A skin lesion imaged with contact-polarized dermoscopy: 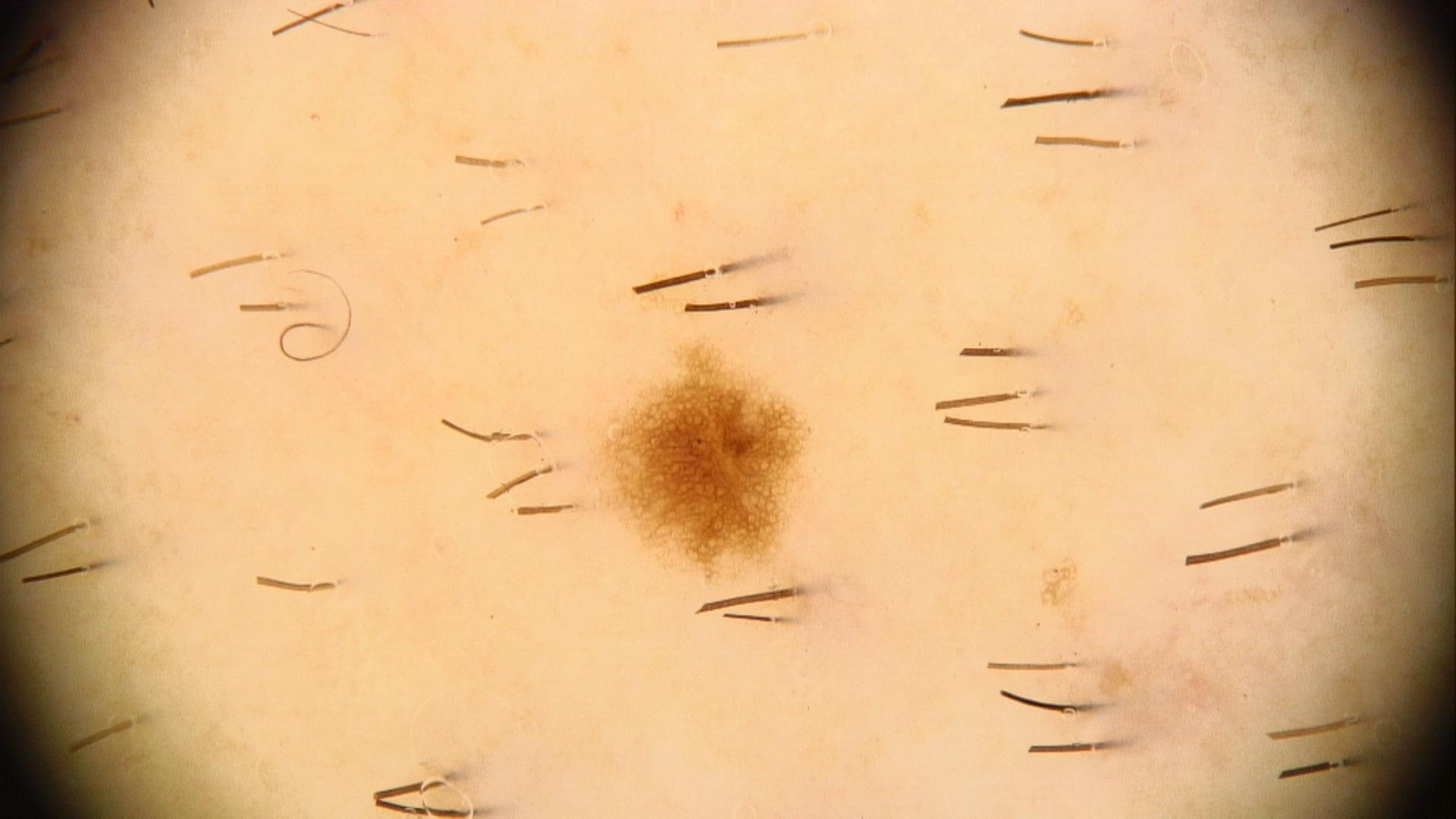The lesion is located on the trunk. The diagnostic impression was a nevus.